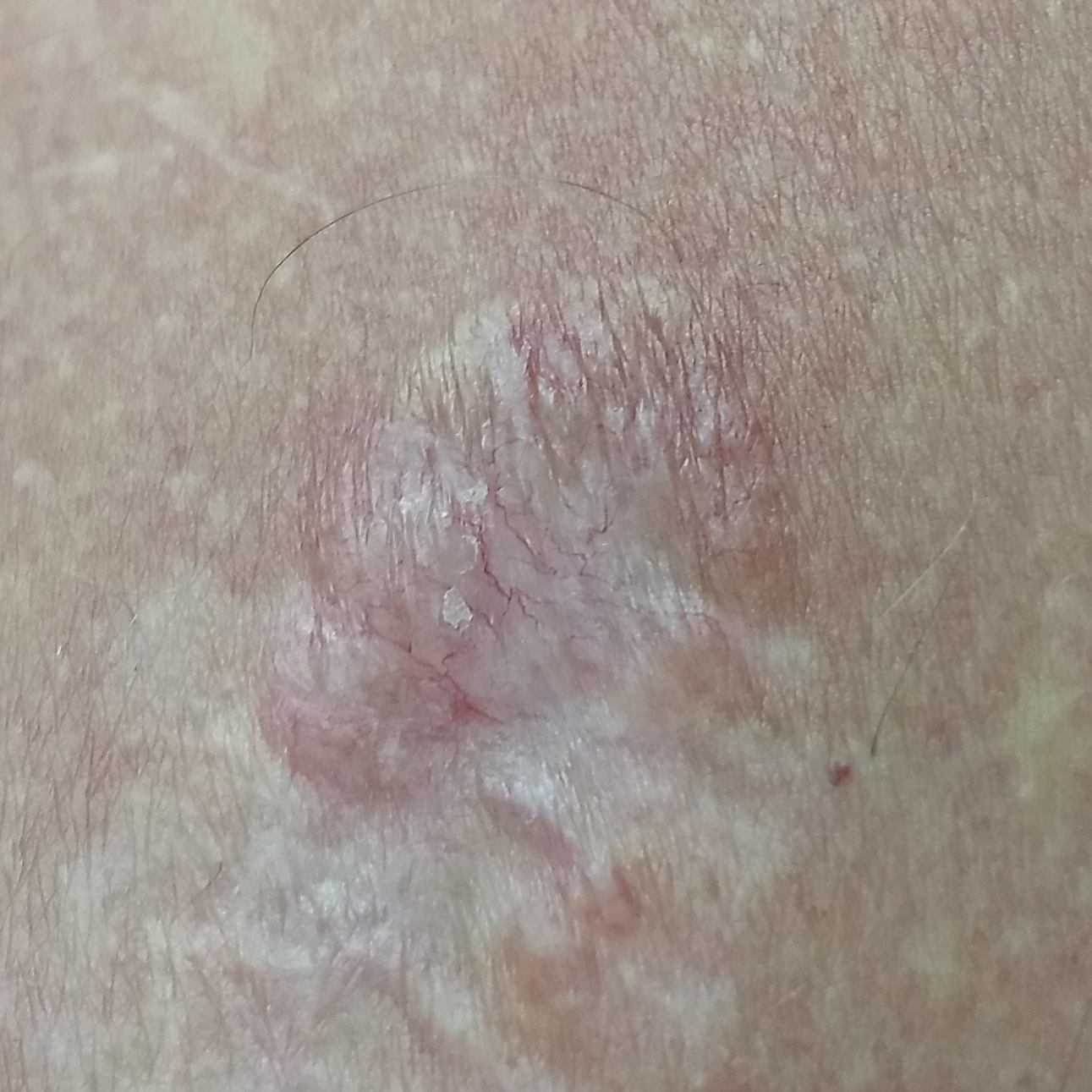<lesion>
  <image>smartphone clinical photo</image>
  <patient>
    <age>55</age>
    <gender>male</gender>
  </patient>
  <lesion_location>the back</lesion_location>
  <diagnosis>
    <name>basal cell carcinoma</name>
    <code>BCC</code>
    <malignancy>malignant</malignancy>
    <confirmation>histopathology</confirmation>
  </diagnosis>
</lesion>